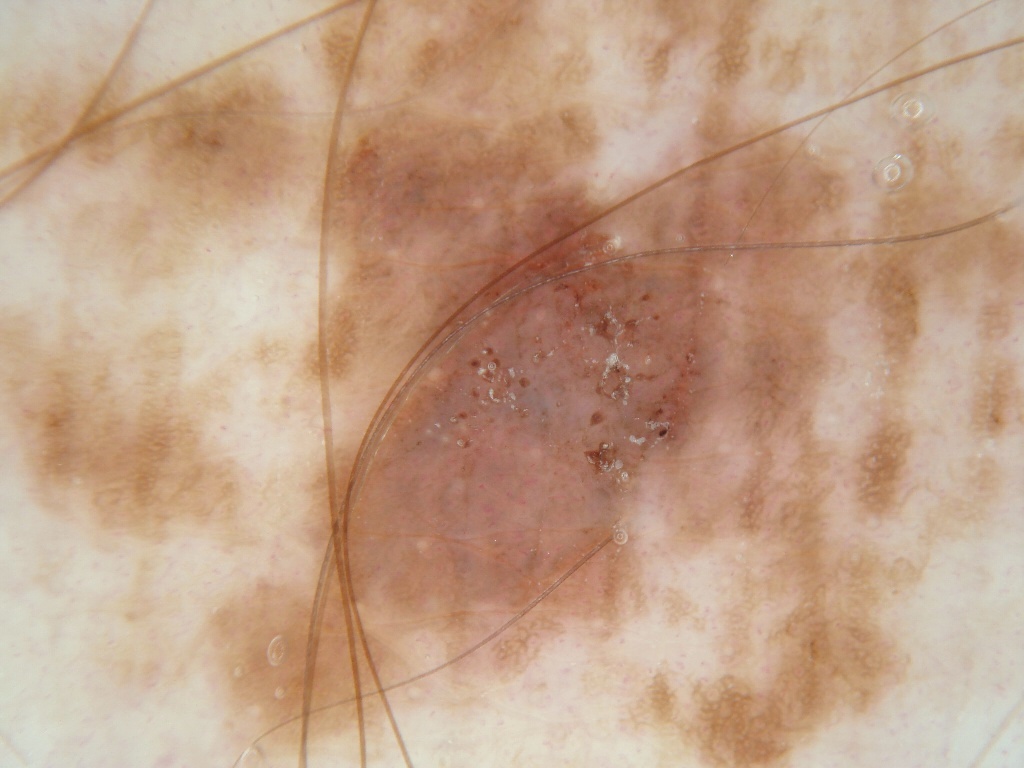A male subject about 55 years old. This is a dermoscopic photograph of a skin lesion. Dermoscopic review identifies milia-like cysts and pigment network. With coordinates (x1, y1, x2, y2), the lesion occupies the region [323, 214, 742, 622]. A moderately sized lesion. The diagnostic assessment was a melanocytic nevus.